A female subject aged 92. On a questionnaire the patient reported a personal history of cancer, a family history of skin cancer, no prior organ transplant, and no immunosuppression — 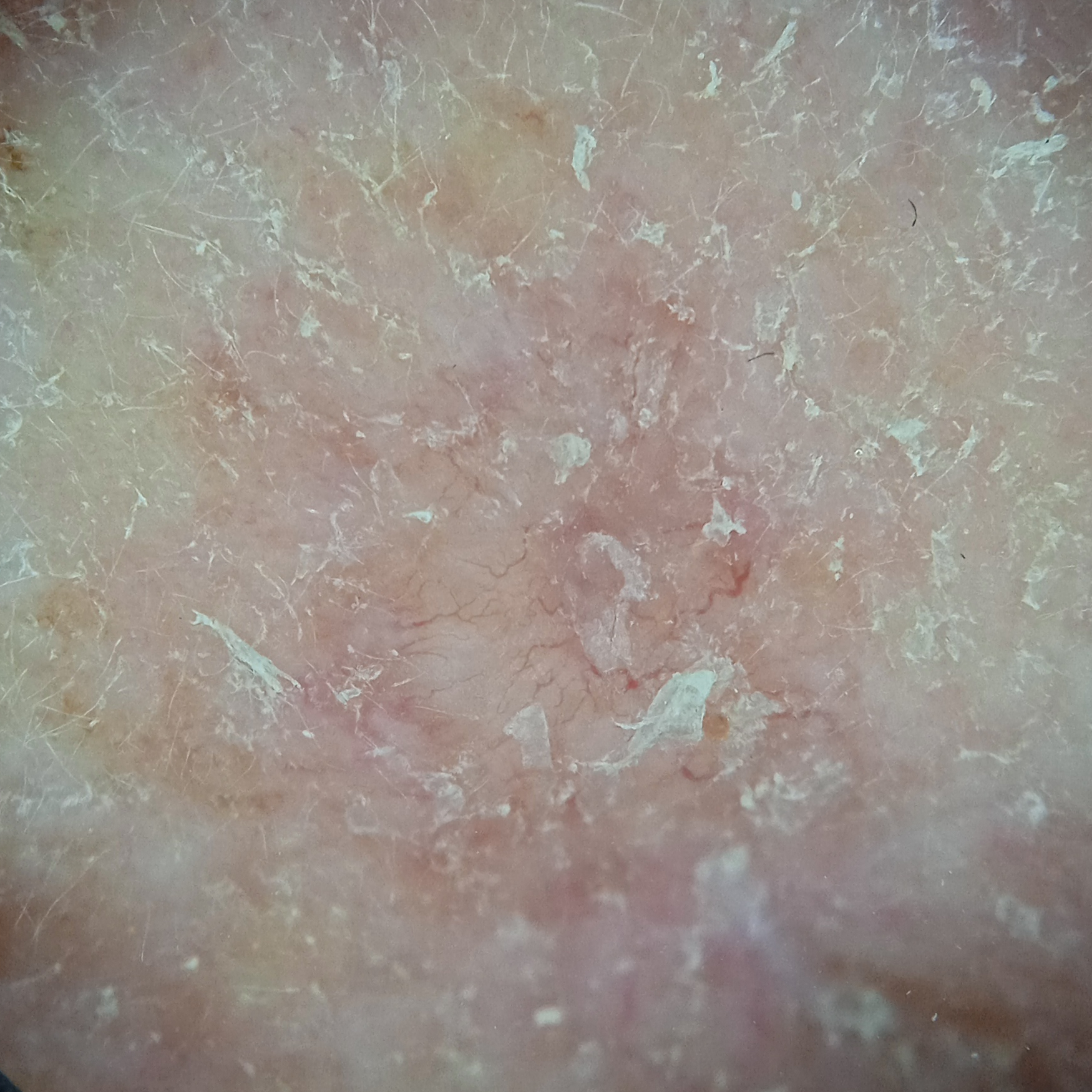Located on the face. The lesion is about 7 mm across. On independent review by four dermatologists, the agreed diagnosis was a basal cell carcinoma.